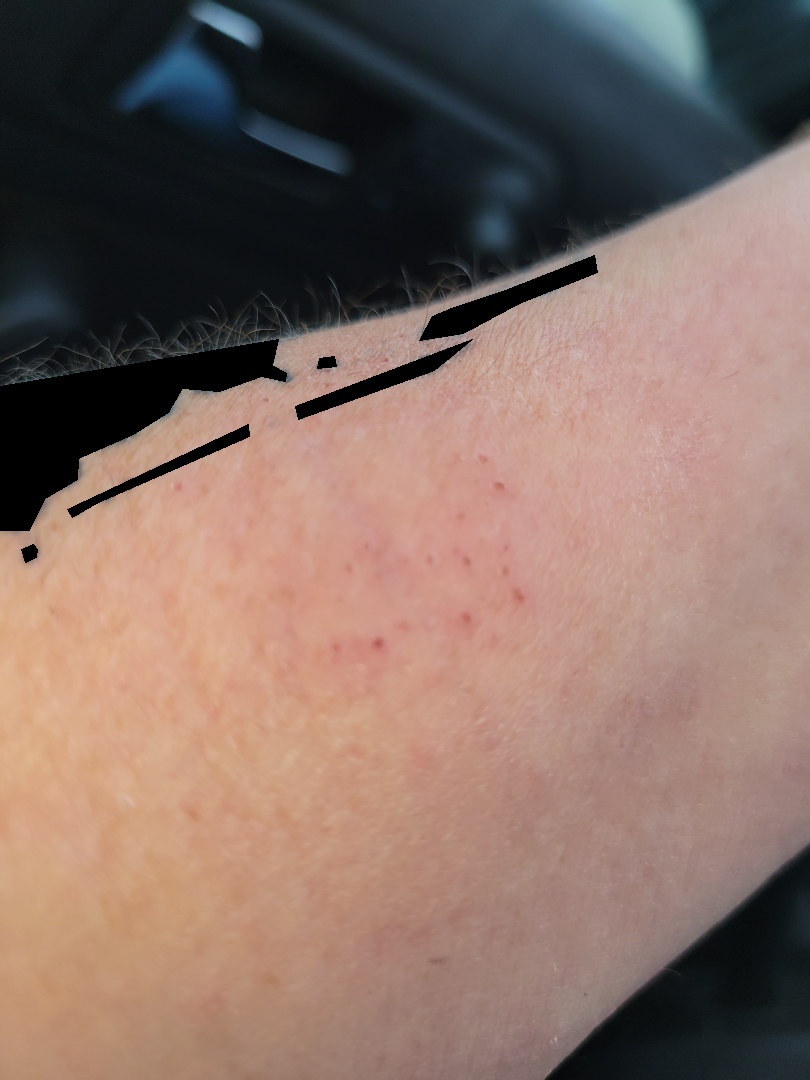Impression: The dermatologist could not determine a likely condition from the photograph alone. History: Female contributor, age 50–59. Located on the arm. The photograph is a close-up of the affected area.